The photograph was taken at an angle:
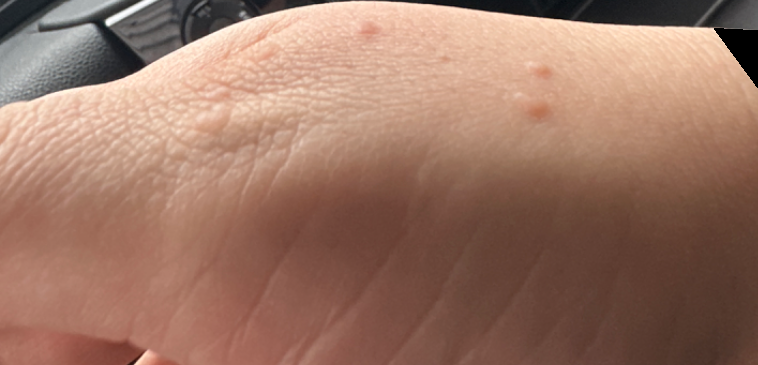Findings: The skin findings could not be characterized from the image.